A dermoscopic close-up of a skin lesion.
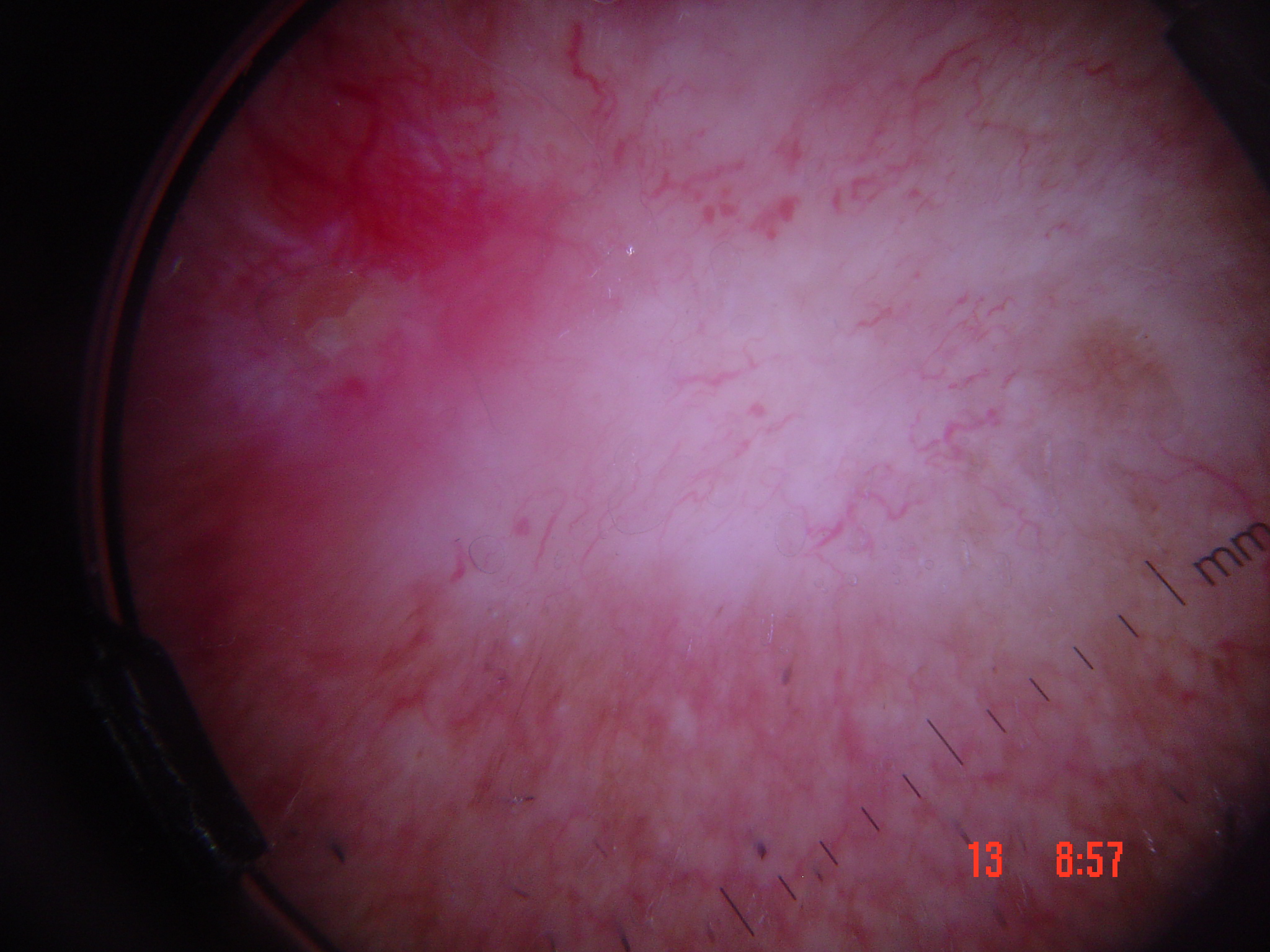The architecture is that of a keratinocytic lesion.
Biopsy-confirmed as a basal cell carcinoma.